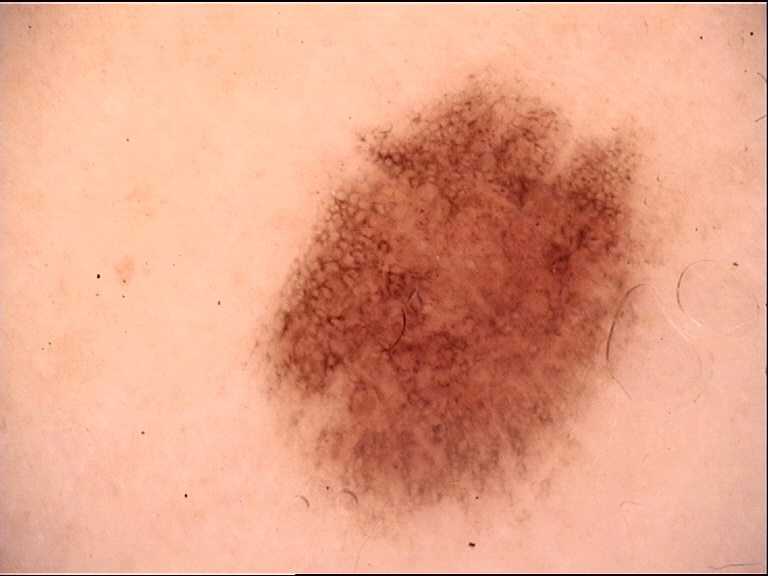imaging: dermoscopy
diagnostic label: dysplastic junctional nevus (expert consensus)